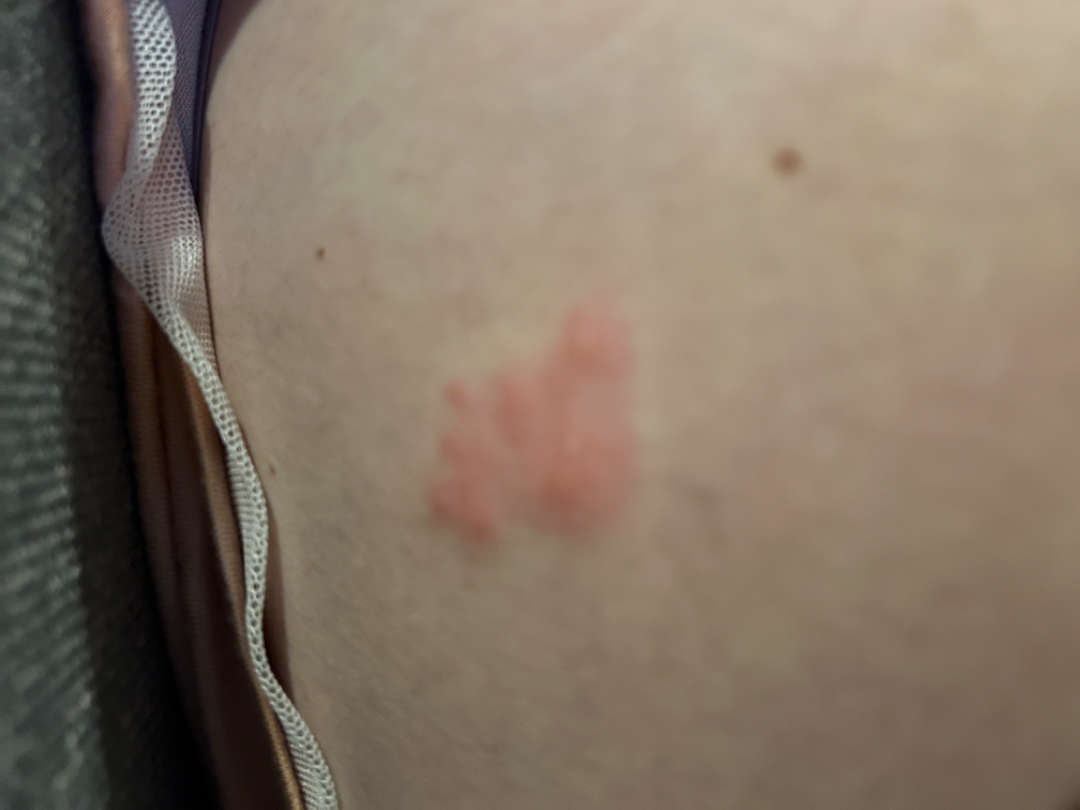assessment: unable to determine